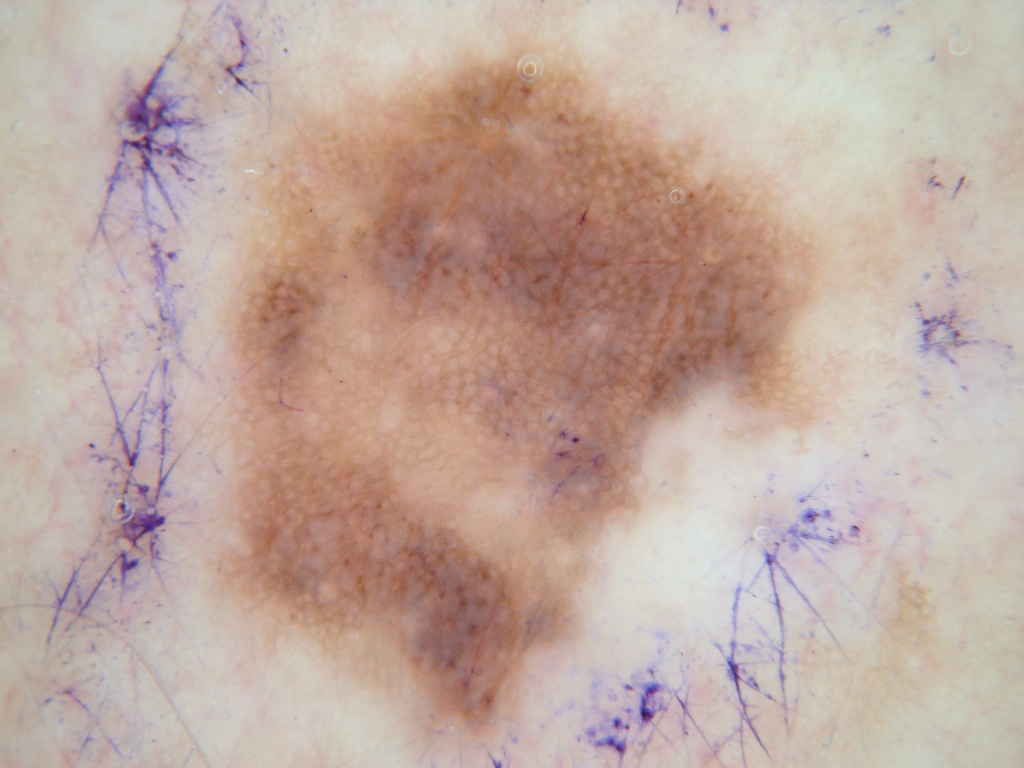Q: What kind of image is this?
A: dermatoscopic image of a skin lesion
Q: What is the lesion's bounding box?
A: [202,37,822,752]
Q: What did the assessment conclude?
A: a benign lesion